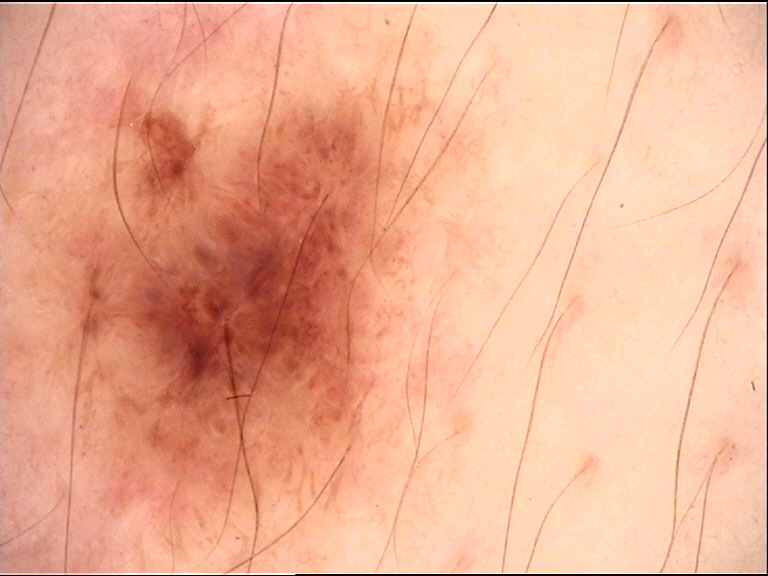Q: What is this lesion?
A: dysplastic junctional nevus (expert consensus)